Reported lesion symptoms include darkening; texture is reported as flat; a close-up photograph — 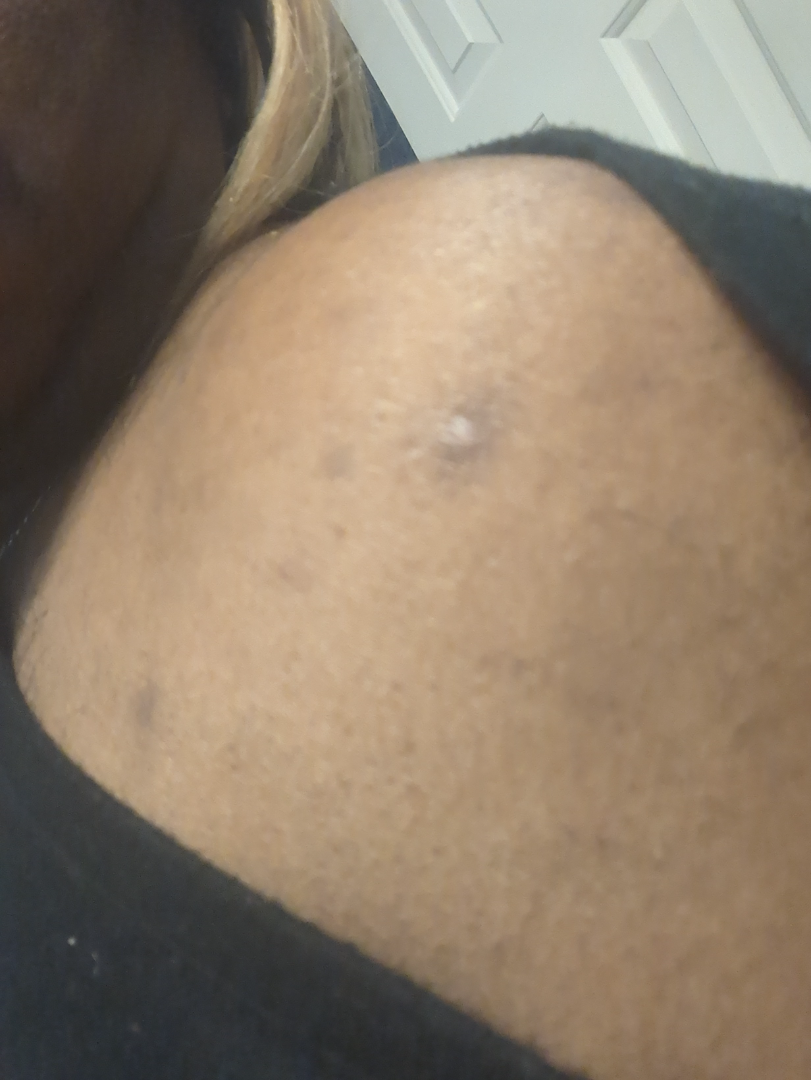assessment = indeterminate